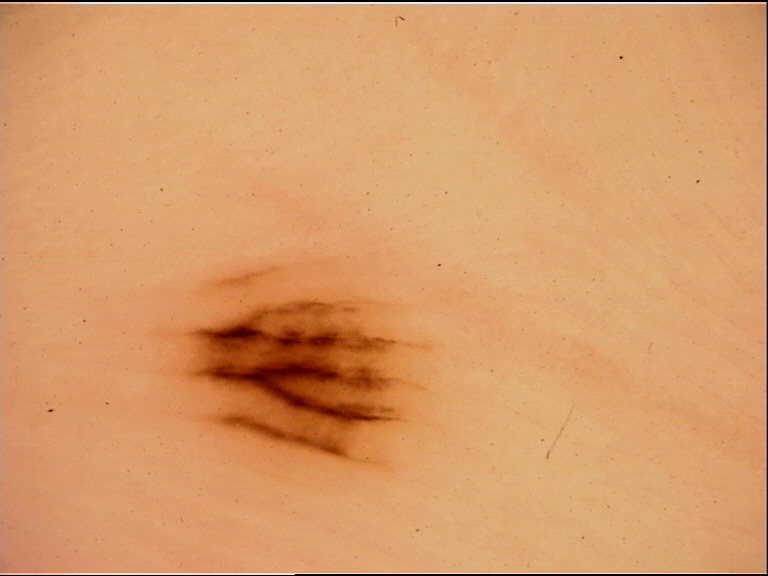Case:
* modality: dermoscopy
* category: banal
* diagnosis: acral junctional nevus (expert consensus)